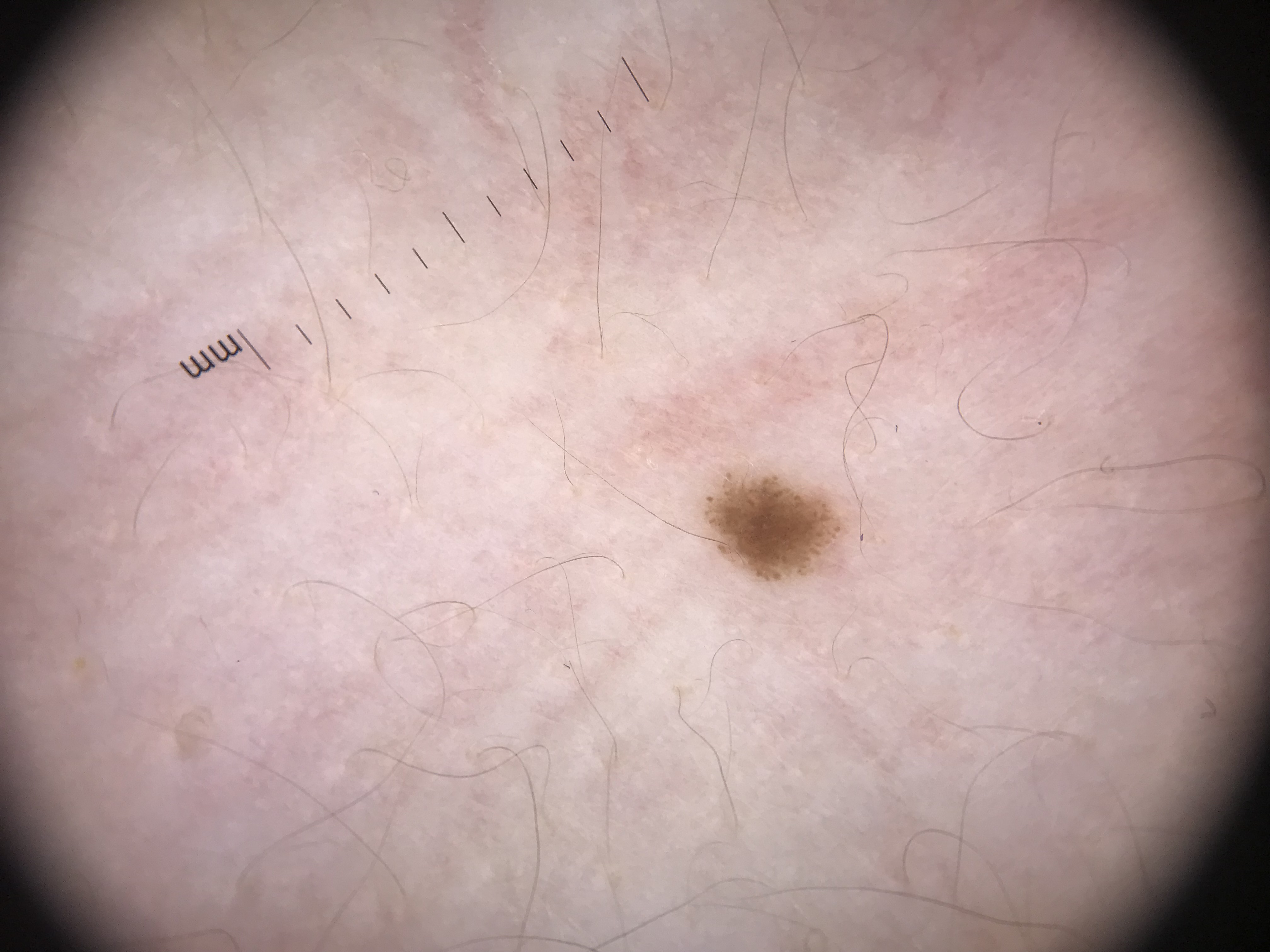Diagnosed as a junctional nevus.